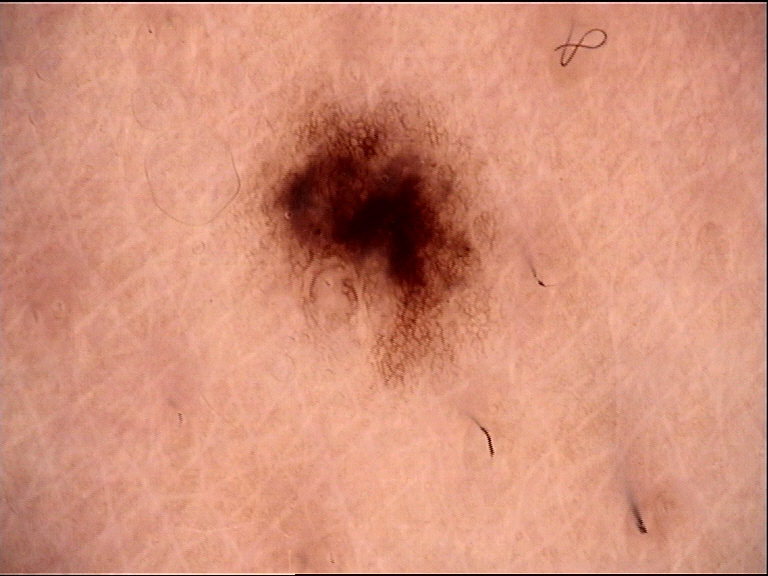A dermoscopy image of a single skin lesion. Consistent with a dysplastic junctional nevus.